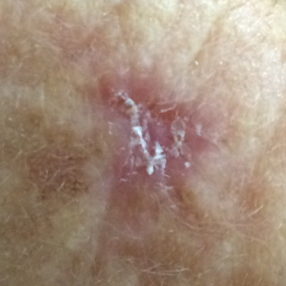Histopathology confirmed a basal cell carcinoma.